The leg is involved. This is a close-up image — 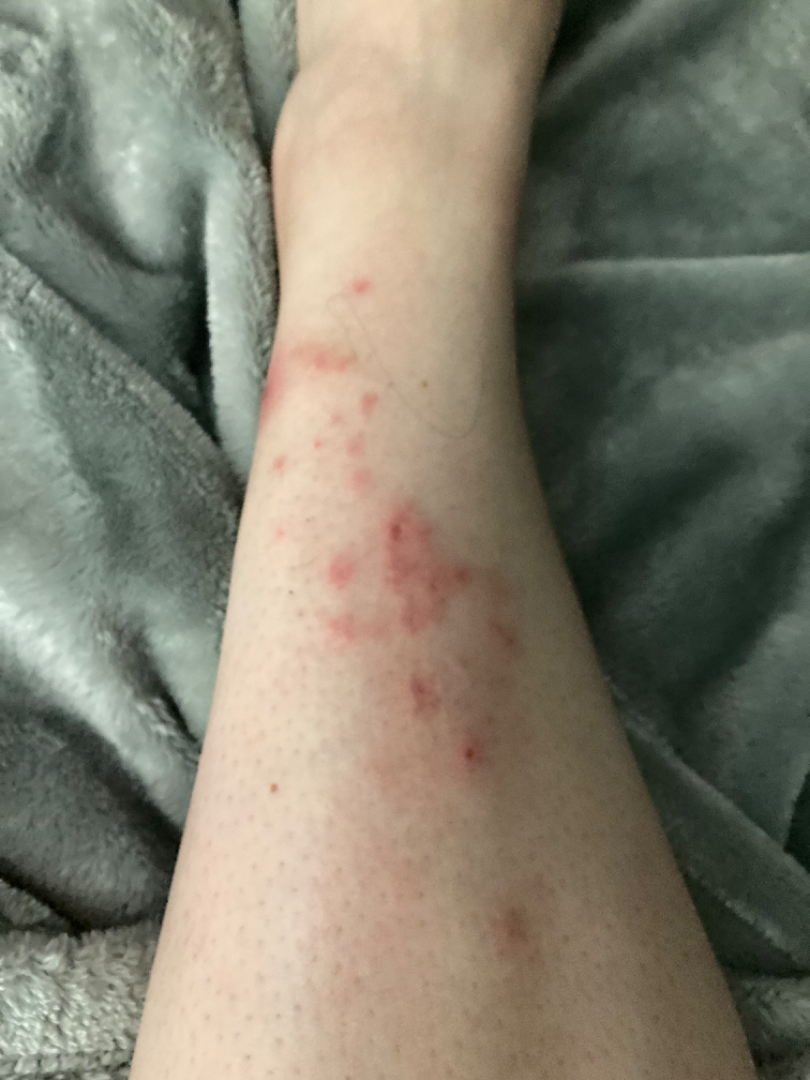One reviewing dermatologist: most likely Eczema; also raised was Pigmented purpuric eruption.